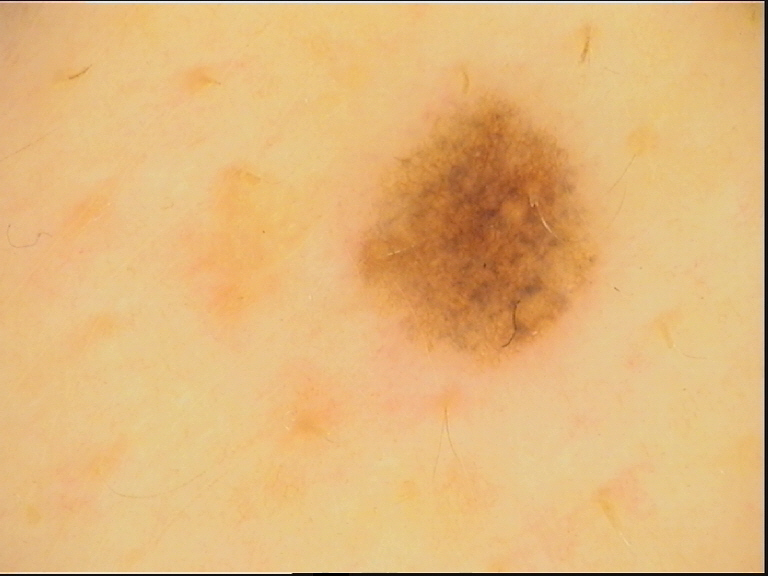Consistent with a benign lesion — a dysplastic junctional nevus.